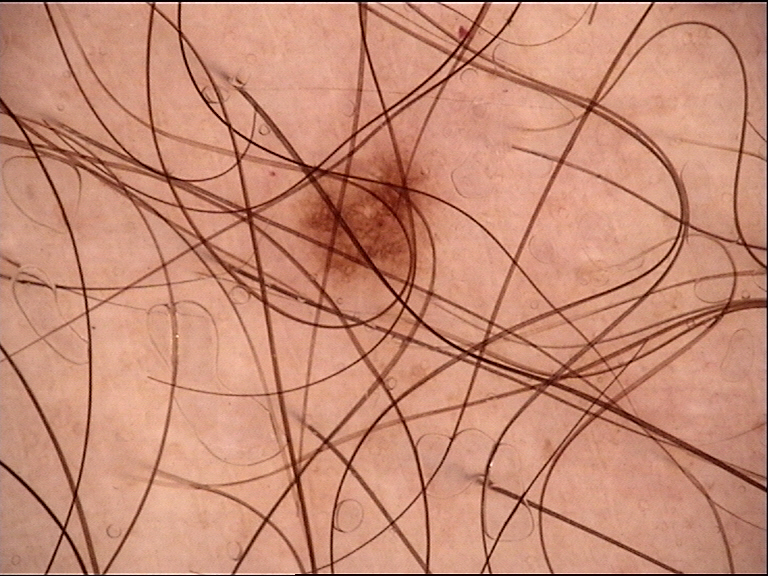Diagnosed as a dysplastic junctional nevus.